A skin lesion imaged with a dermatoscope.
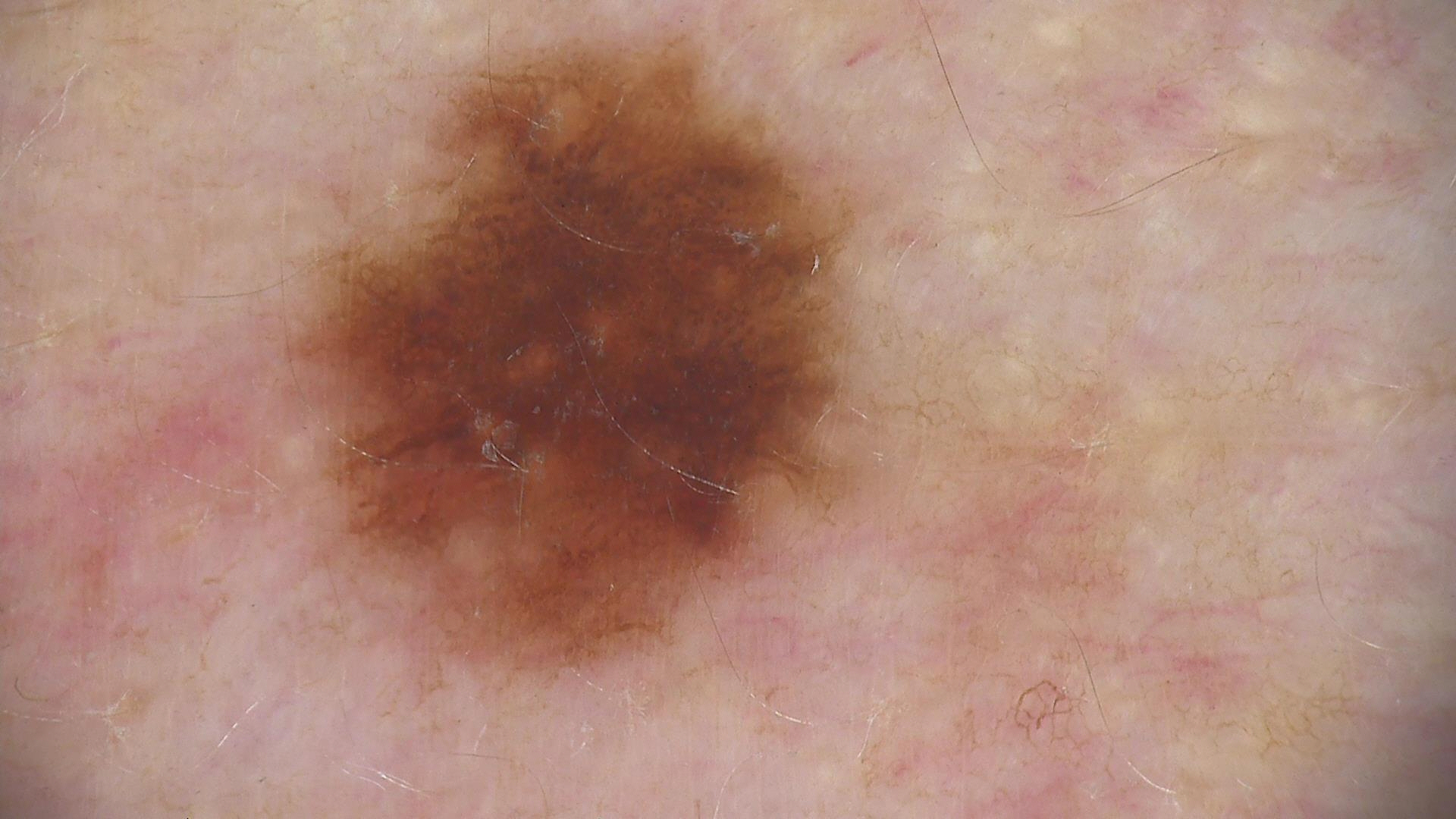Diagnosed as a benign lesion — a dysplastic junctional nevus.